Dermoscopy of a skin lesion, a male patient in their mid-40s: 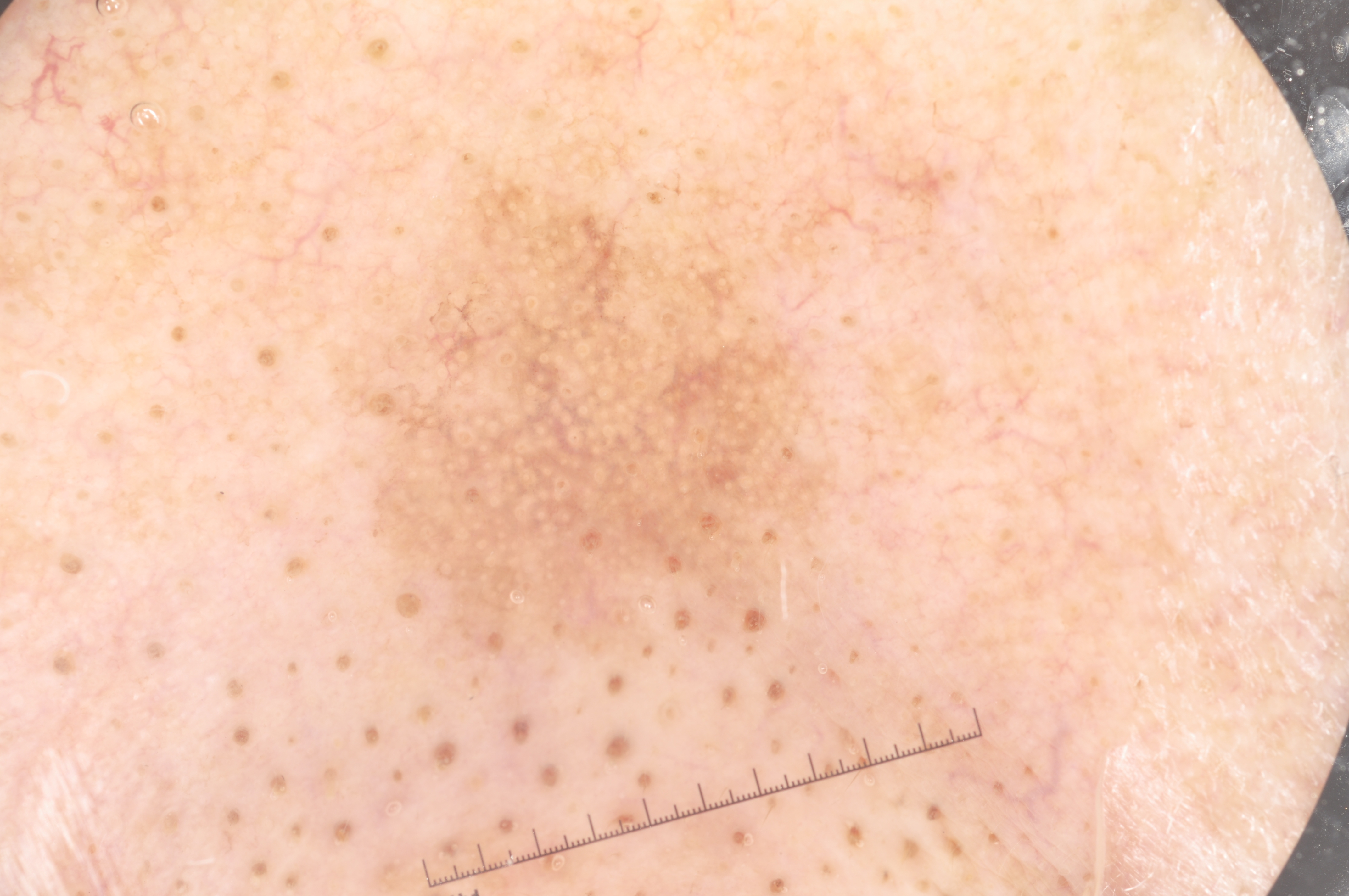Case summary:
– dermoscopic features not present · milia-like cysts, pigment network, negative network, and streaks
– lesion size · ~19% of the field
– bounding box · left=303, top=150, right=861, bottom=682
– impression · a melanoma